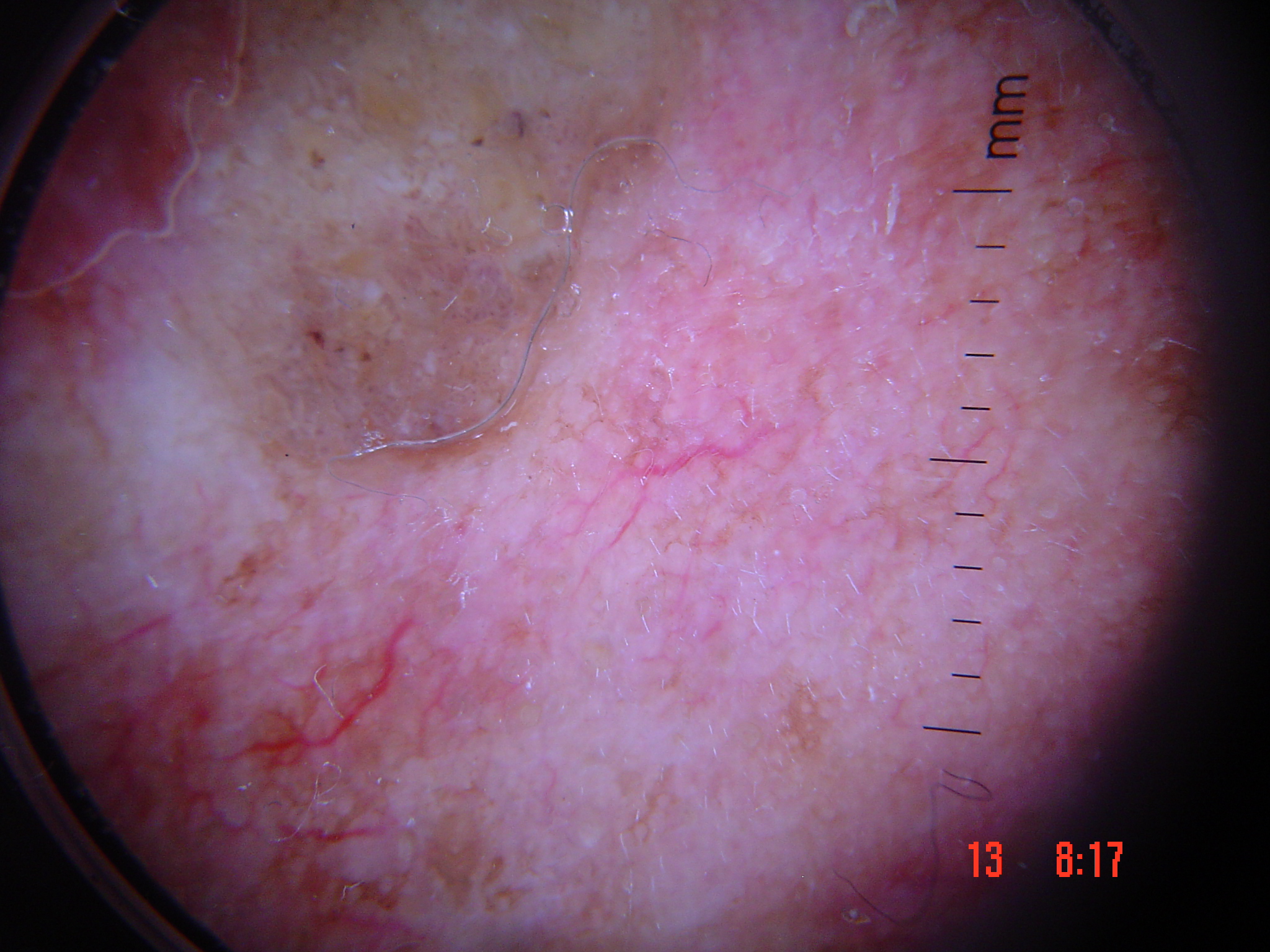Summary:
A dermoscopic photograph of a skin lesion.
Conclusion:
Consistent with a keratinocytic lesion — a seborrheic keratosis.